A clinical photograph of a skin lesion. A female subject in their mid-50s. The patient is Fitzpatrick skin type II. History notes pesticide exposure — 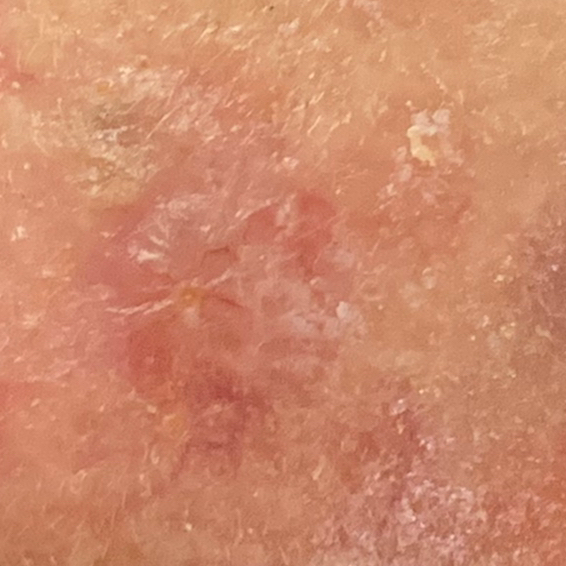The lesion was found on the nose.
Measuring about 6 × 5 mm.
The patient reports that the lesion itches.
Histopathology confirmed an actinic keratosis.